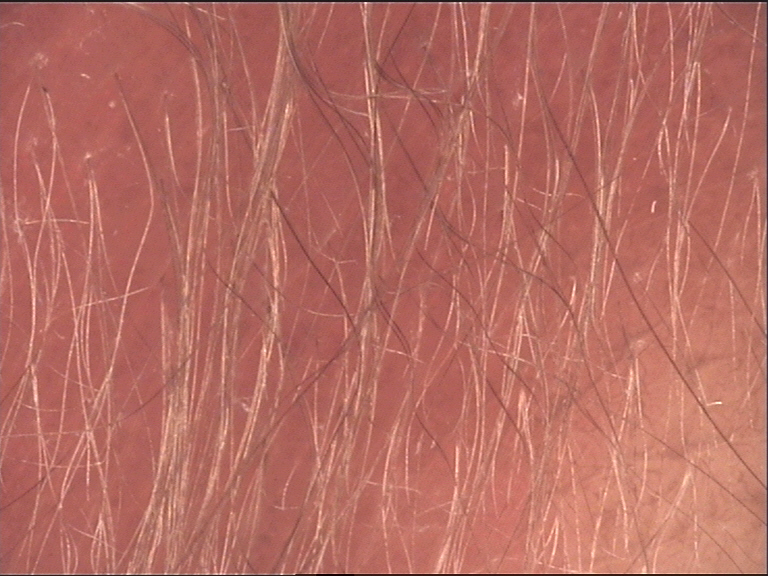{
  "image": "dermoscopy",
  "lesion_type": {
    "main_class": "banal",
    "pattern": "junctional"
  },
  "diagnosis": {
    "name": "congenital junctional nevus",
    "code": "cjb",
    "malignancy": "benign",
    "super_class": "melanocytic",
    "confirmation": "expert consensus"
  }
}